This image was taken at a distance:
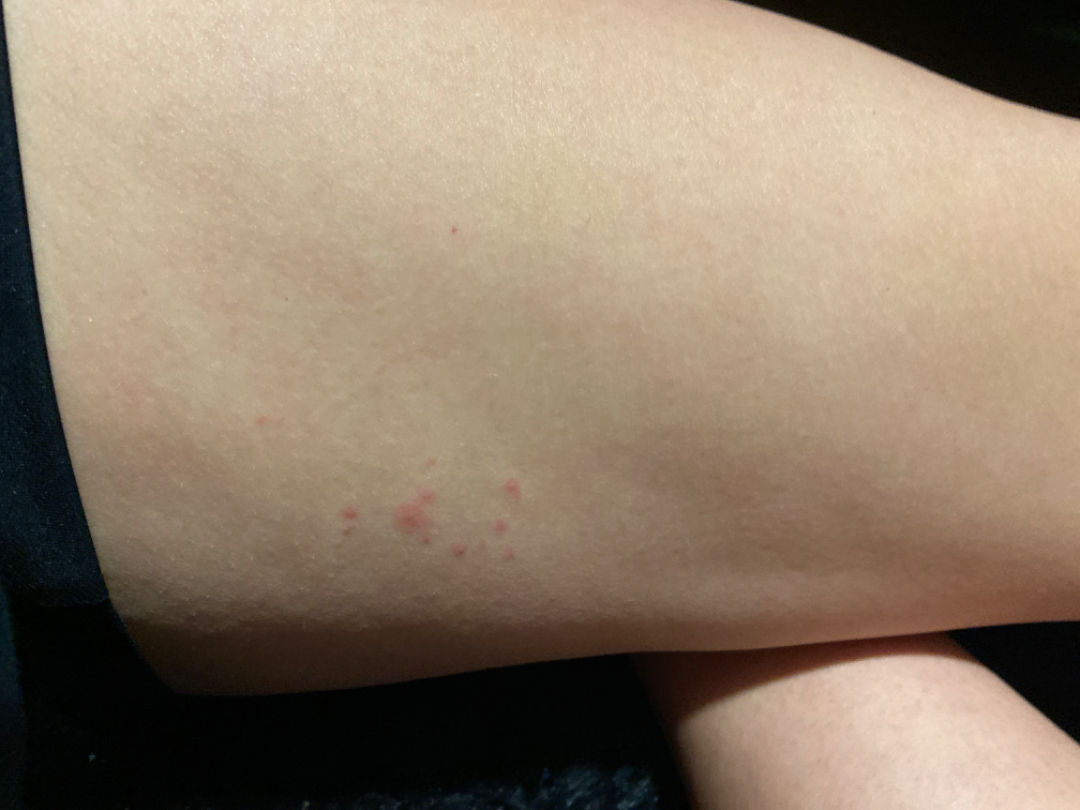assessment=a single dermatologist reviewed the case: the differential, in no particular order, includes Urticaria, Insect Bite and Hypersensitivity.